The patient is a female aged 43-47, a dermoscopic view of a skin lesion: 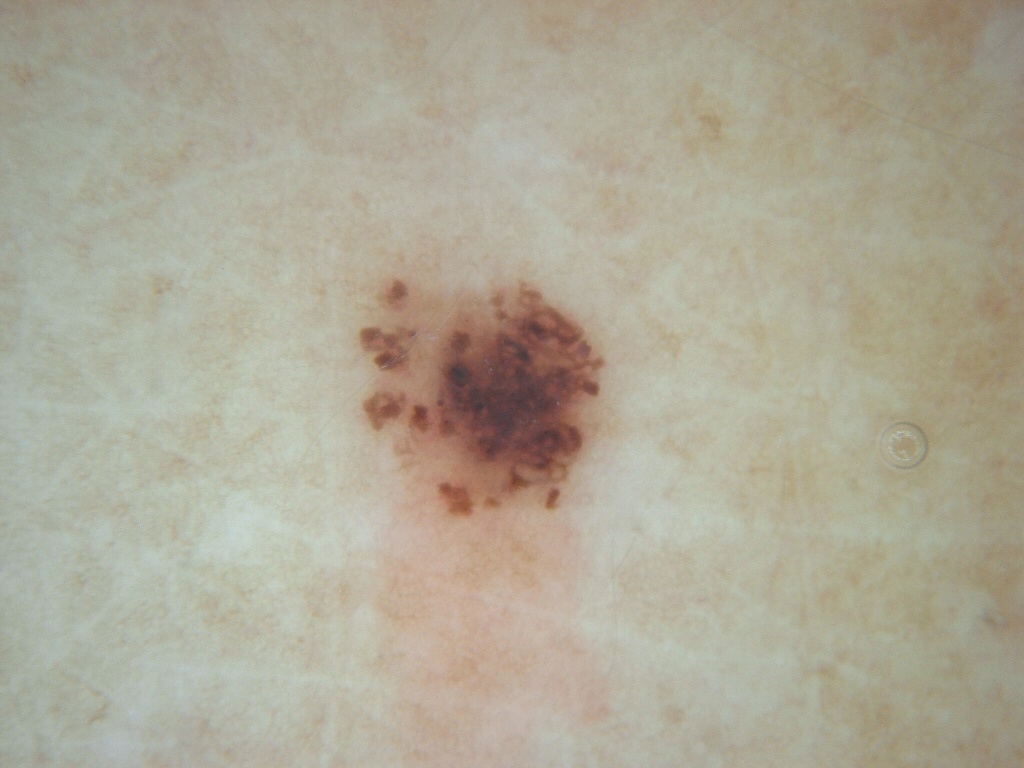Q: Which dermoscopic features were noted?
A: pigment network
Q: Where is the lesion located?
A: bbox(357, 276, 603, 522)
Q: How much of the field does the lesion occupy?
A: ~6% of the field
Q: What did the assessment conclude?
A: a melanocytic nevus, a benign skin lesion